The contributor is 40–49, female. This is a close-up image.
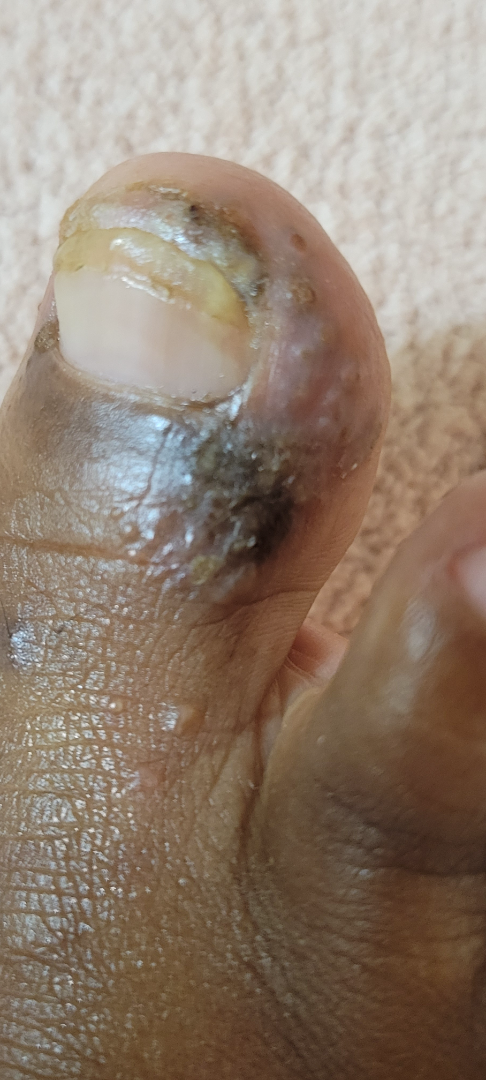Herpes Simplex and Eczema were each considered, in no particular order; less probable is Tinea.